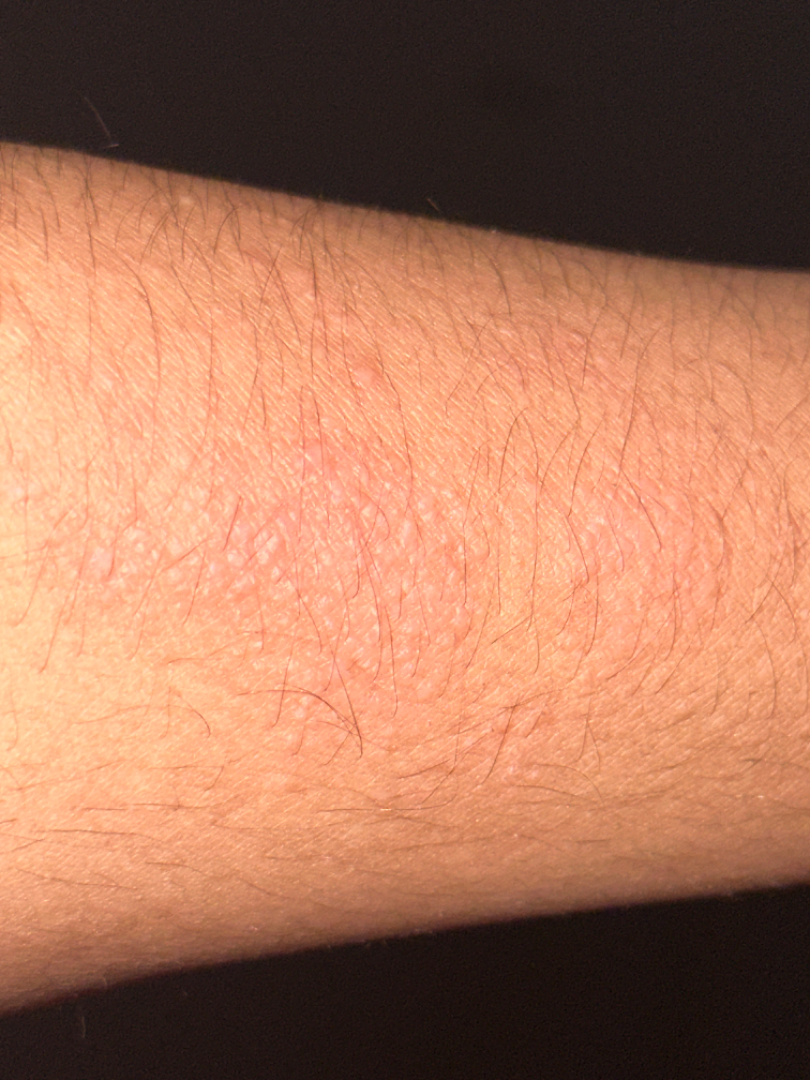contributor: female | skin tone: lay graders estimated Monk Skin Tone 2 (US pool) or 3 (India pool) | present for: one to three months | site: arm | image framing: at an angle | lesion symptoms: itching and enlargement | surface texture: raised or bumpy | self-categorized as: a nail problem | dermatologist impression: most consistent with Allergic Contact Dermatitis; also consider Acute and chronic dermatitis; the differential also includes Eczema; less likely is Lichen nitidus.